The patient describes having a moderate number of moles; collected as part of a research study, without a referral diagnosis; a clinical photograph showing a skin lesion; the patient says their skin reddens painfully with sun exposure; a female subject aged 81:
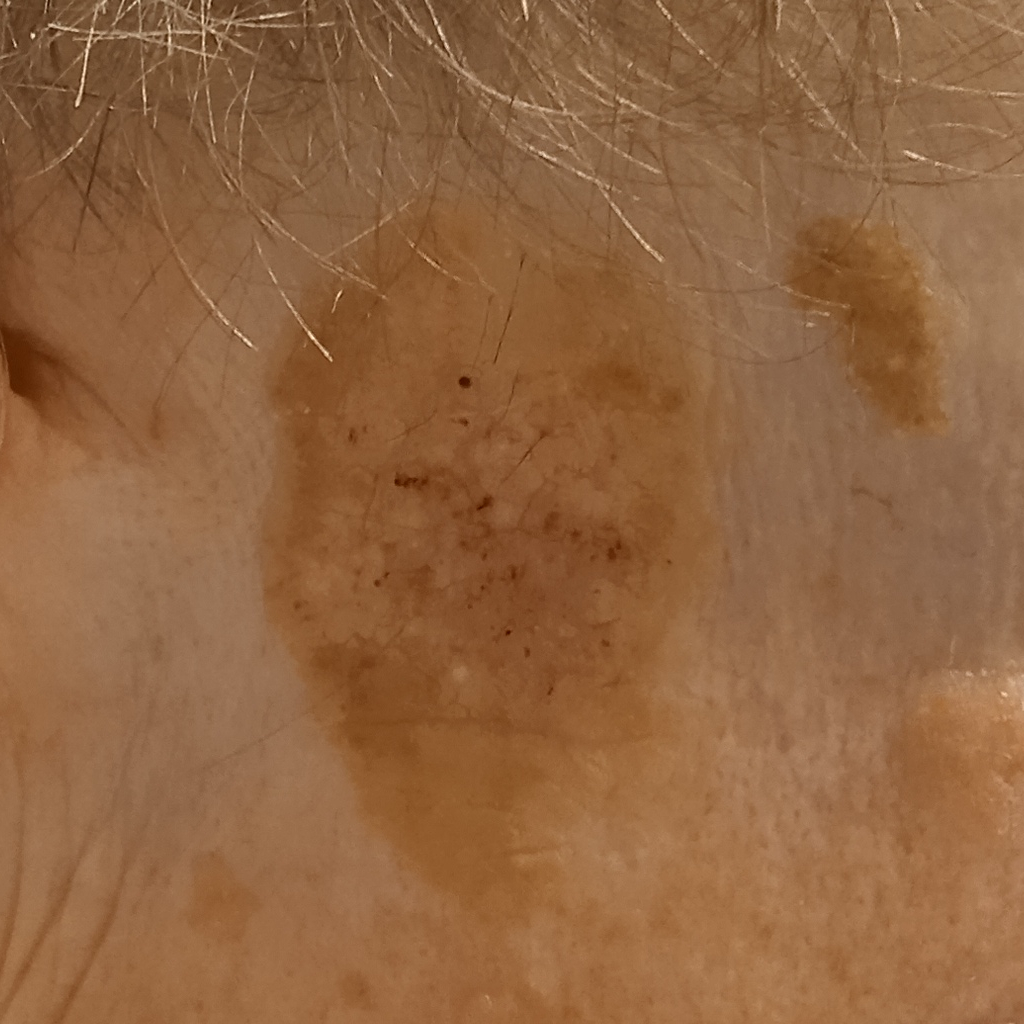Case summary: The lesion is on the face. Measuring roughly 36.6 mm. Impression: The dermatologists' assessment was a seborrheic keratosis.